A close-up photograph. The back of the torso is involved. Male subject, age 18–29:
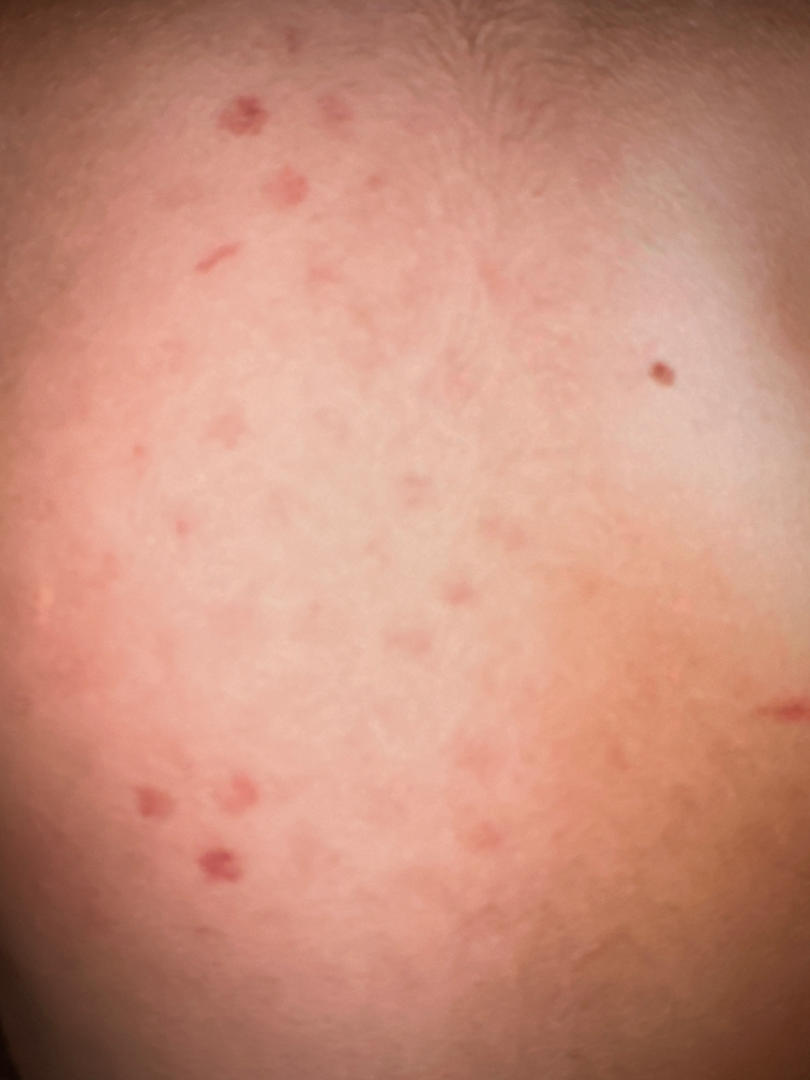Impression: The reviewer was unable to grade this case for skin condition.